Texture is reported as raised or bumpy; Fitzpatrick phototype II; the patient described the issue as a rash; reported lesion symptoms include itching; an image taken at a distance; present for less than one week; the patient is 60–69, female; the lesion involves the arm: 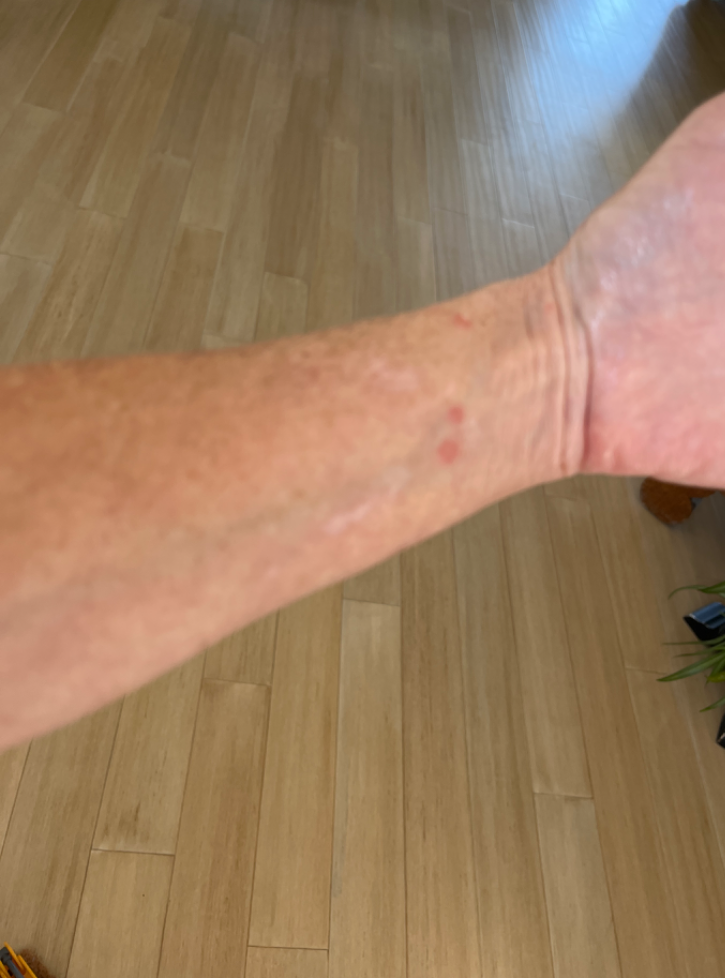{"differential": {"leading": ["Insect Bite"], "unlikely": ["Allergic Contact Dermatitis"]}}